A skin lesion imaged with a dermatoscope.
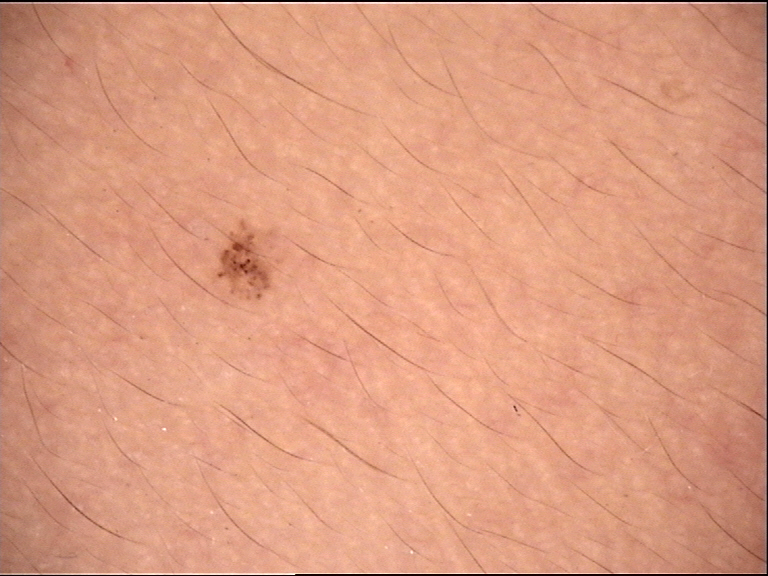- lesion type: banal
- diagnosis: junctional nevus (expert consensus)